A dermoscopic close-up of a skin lesion: 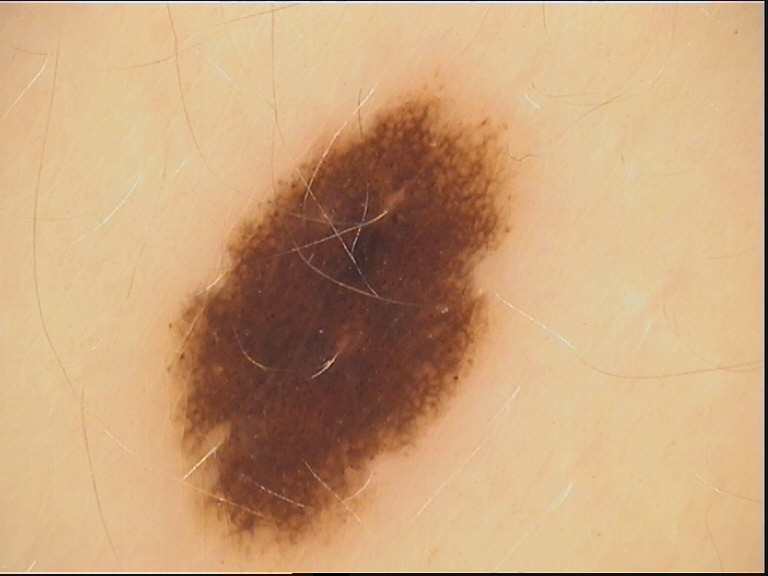diagnosis: dysplastic junctional nevus (expert consensus).